The subject is a female aged 40–49 · the affected area is the top or side of the foot and leg · this image was taken at an angle.
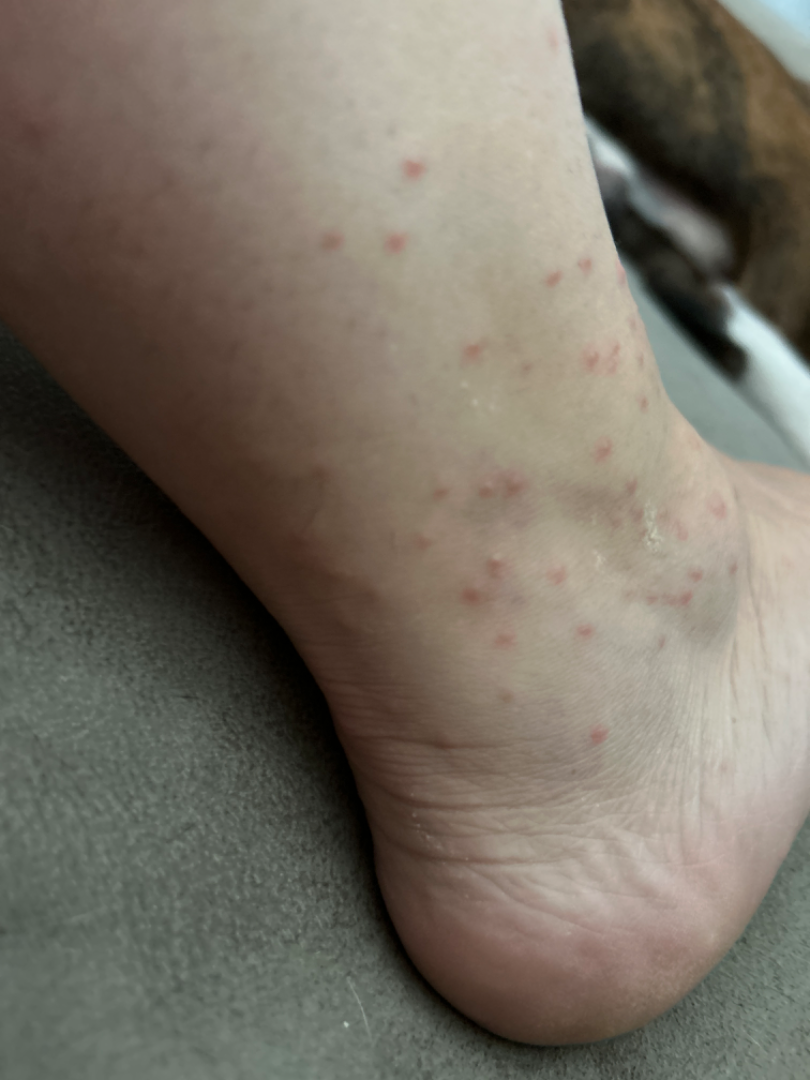The contributor notes the condition has been present for one to four weeks.
Texture is reported as raised or bumpy.
The patient described the issue as skin that appeared healthy to them.
Reported lesion symptoms include itching, burning, bothersome appearance and pain.
Insect Bite (weight 1.00).